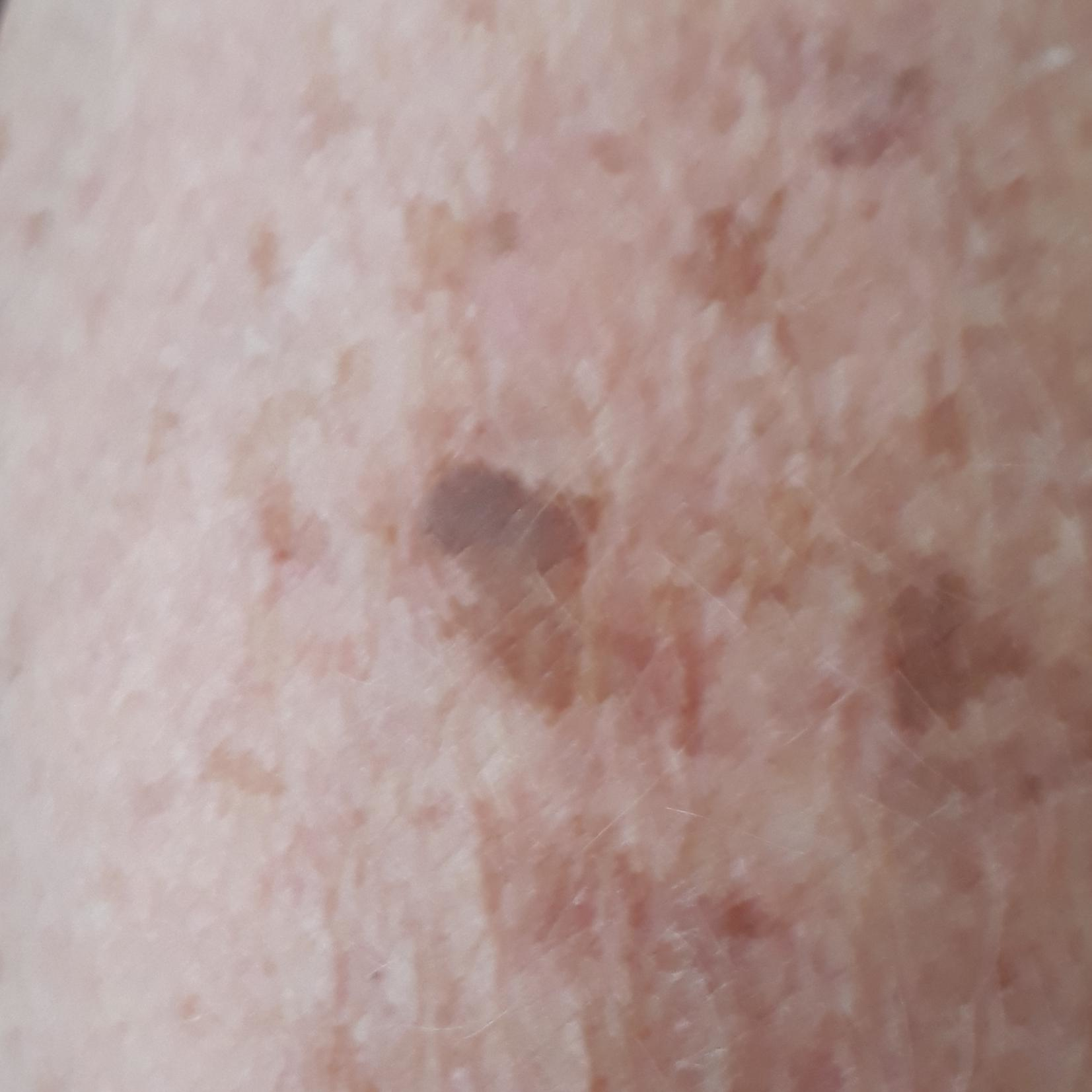diagnosis = seborrheic keratosis (clinical consensus).